A dermatoscopic image of a skin lesion:
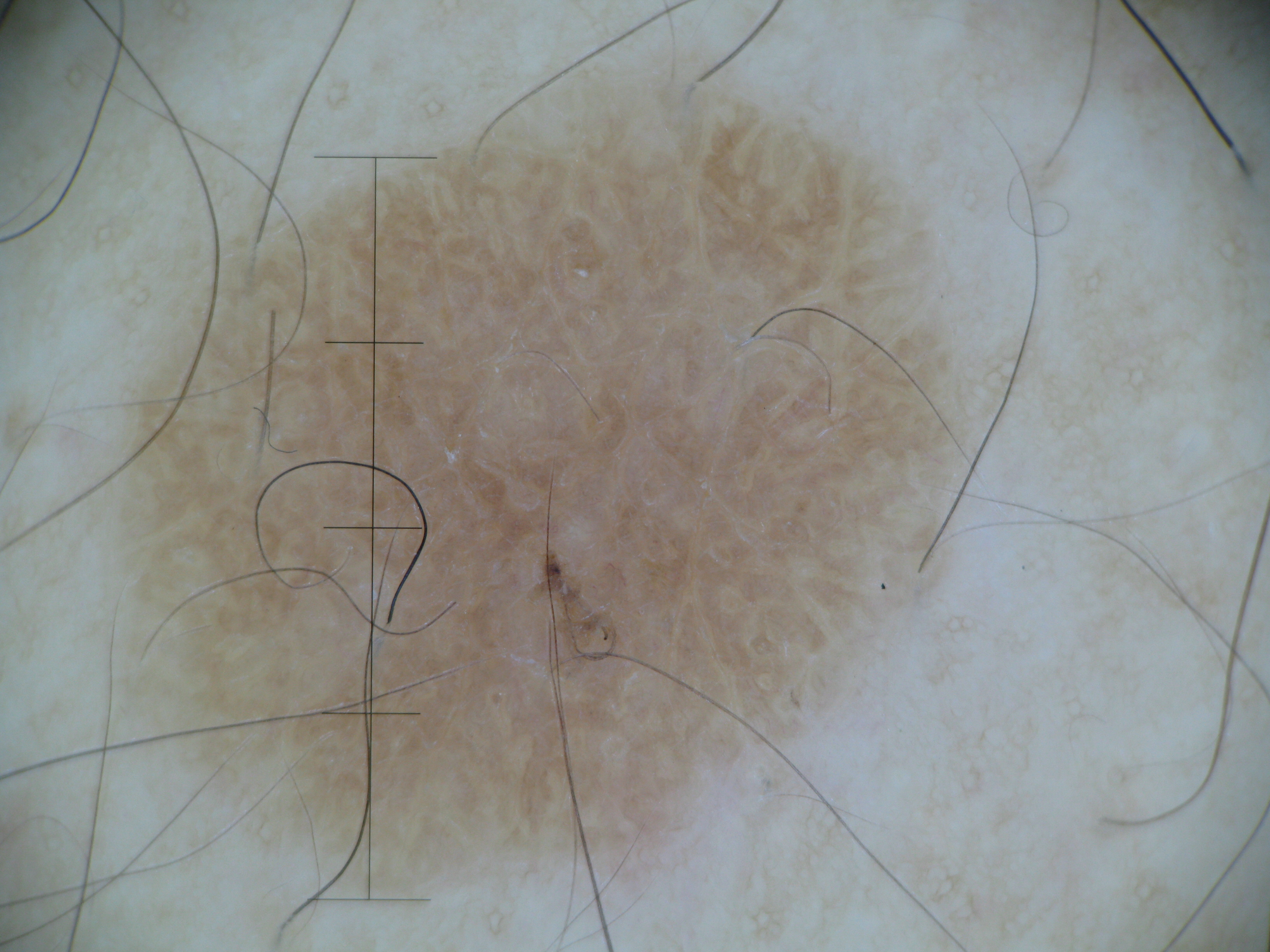<case>
<diagnosis>
<name>seborrheic keratosis</name>
<code>sk</code>
<malignancy>benign</malignancy>
<super_class>non-melanocytic</super_class>
<confirmation>expert consensus</confirmation>
</diagnosis>
</case>